The patient is a female about 35 years old · this is a dermoscopic photograph of a skin lesion:
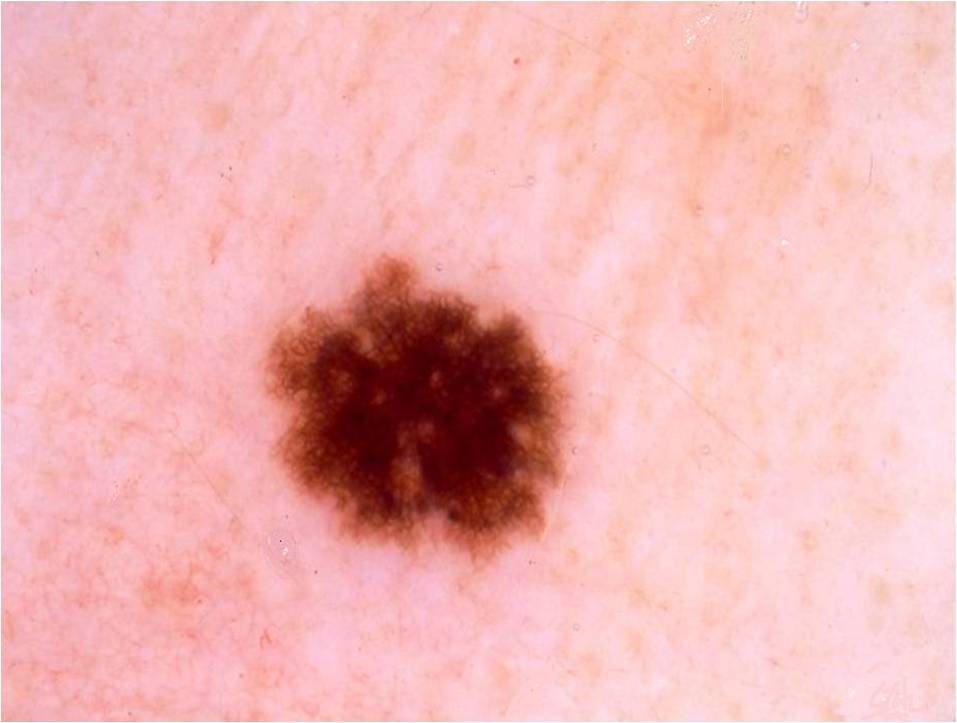<lesion>
  <lesion_location>
    <bbox_xyxy>261, 252, 568, 566</bbox_xyxy>
  </lesion_location>
  <dermoscopic_features>
    <present>pigment network</present>
    <absent>milia-like cysts, streaks, globules, negative network</absent>
  </dermoscopic_features>
  <lesion_extent>moderate</lesion_extent>
  <diagnosis>
    <name>melanocytic nevus</name>
    <malignancy>benign</malignancy>
    <lineage>melanocytic</lineage>
    <provenance>clinical</provenance>
  </diagnosis>
</lesion>